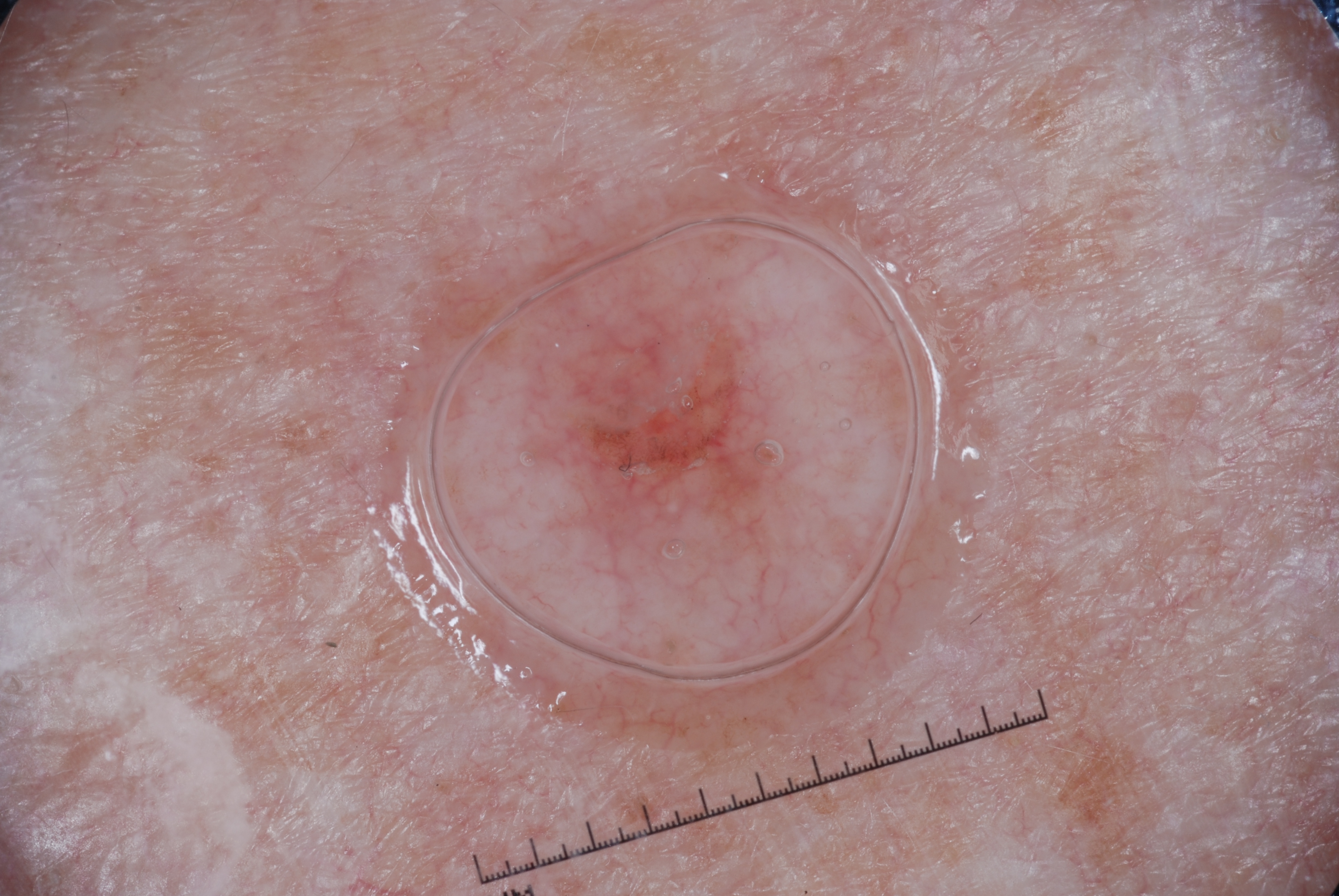{
  "image": {
    "modality": "dermoscopy"
  },
  "lesion_location": {
    "bbox_xyxy": [
      539,
      292,
      801,
      515
    ]
  },
  "diagnosis": {
    "name": "melanocytic nevus",
    "malignancy": "benign",
    "lineage": "melanocytic",
    "provenance": "clinical"
  }
}